A male subject approximately 40 years of age · Fitzpatrick skin type III · the chart documents a first-degree relative with melanoma: 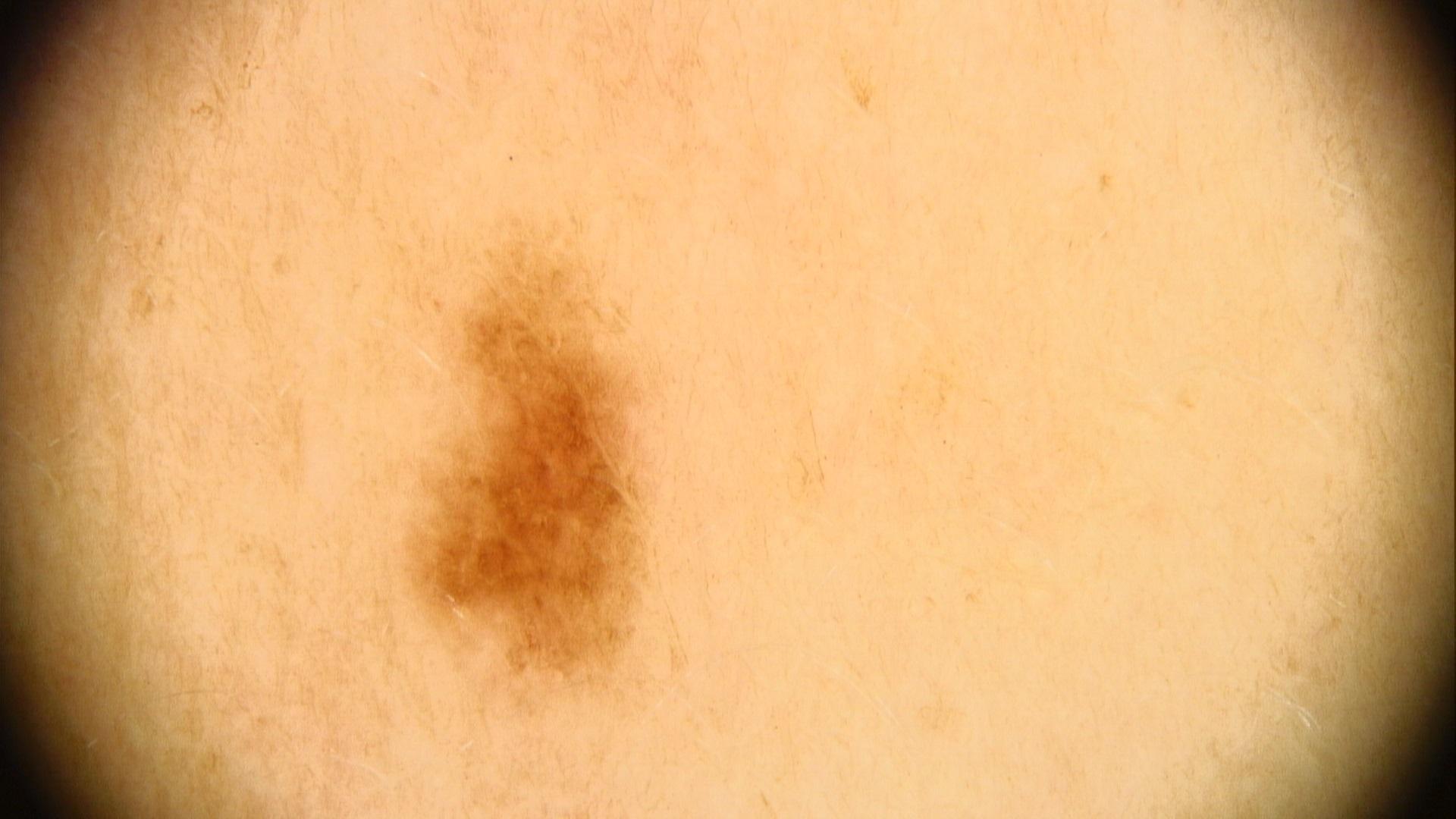| key | value |
|---|---|
| site | the posterior trunk |
| assessment | Nevus |